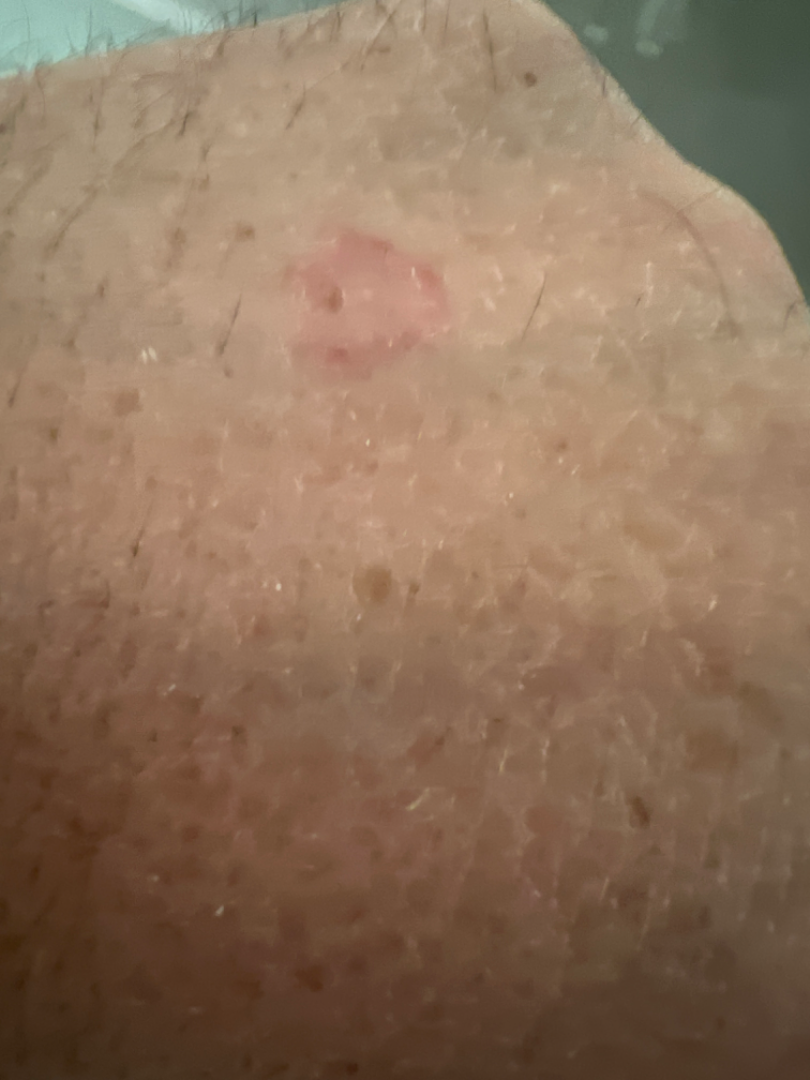Q: What is the patient's skin tone?
A: human graders estimated 3 on the MST
Q: Image view?
A: at an angle
Q: What is the differential diagnosis?
A: a single dermatologist reviewed the case: most consistent with Eczema; possibly Tinea